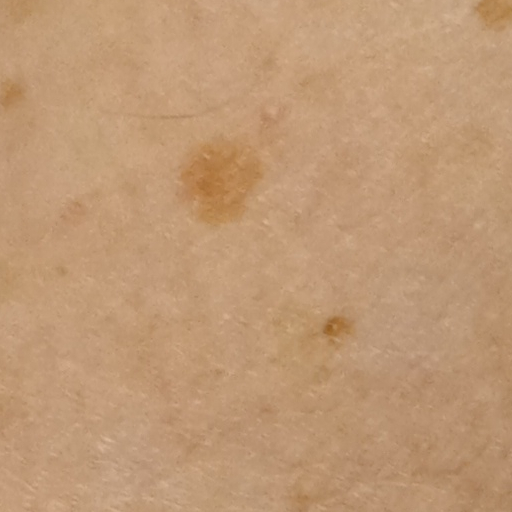Findings: A female patient age 71. Few moles overall by the patient's own estimate. The patient says their skin reddens with sun exposure. The patient reports a personal history of skin cancer and a personal history of cancer. A clinical photograph showing a skin lesion. Imaged for a research study, with no referral diagnosis recorded. The lesion involves an arm. Measuring roughly 1.7 mm. Impression: Dermatologist review favored a melanocytic nevus.